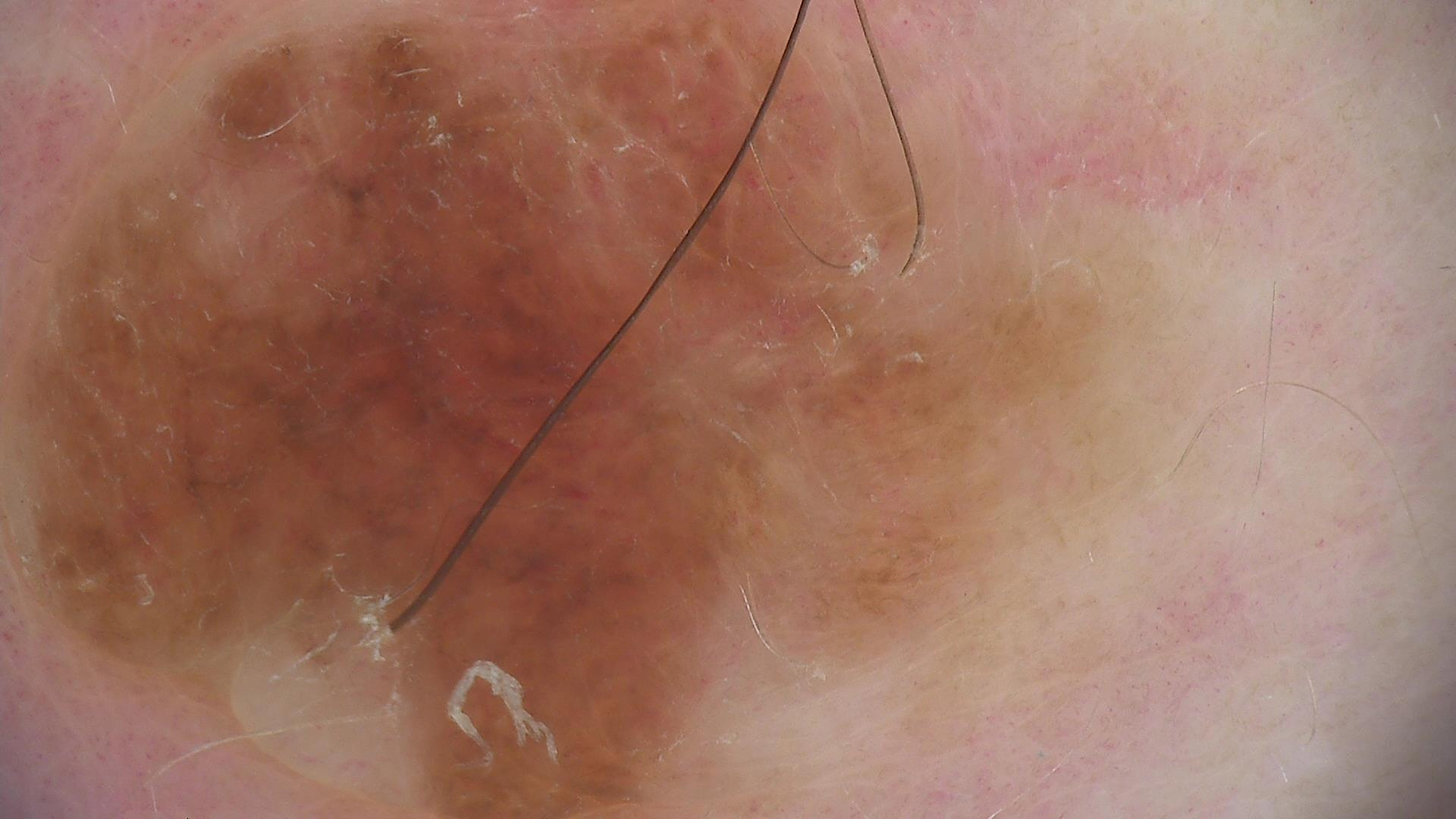imaging = dermoscopy
subtype = banal
label = congenital compound nevus (expert consensus)